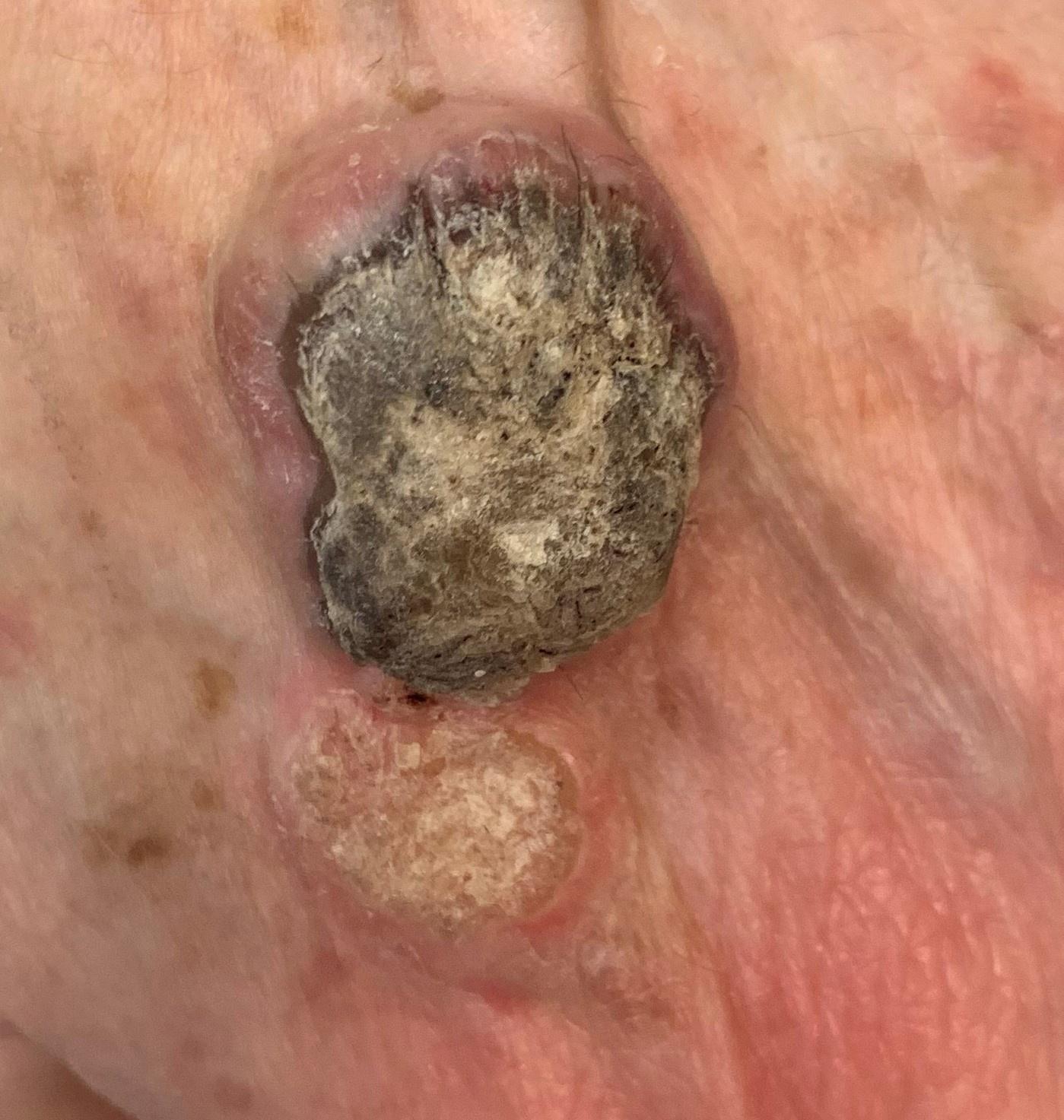FST — II
image — clinical photograph
body site — an upper extremity
pathology — Squamous cell carcinoma (biopsy-proven)